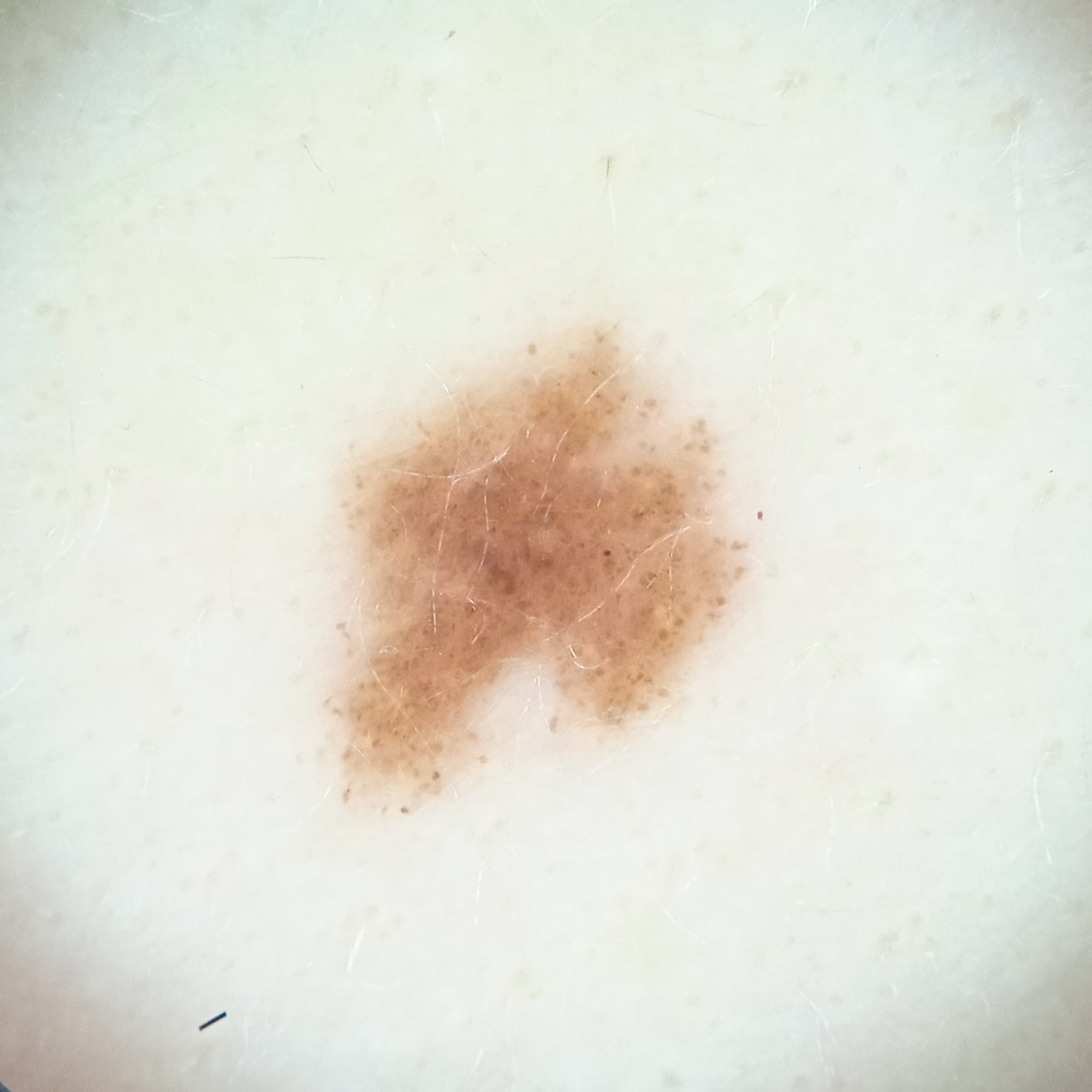Case summary:
The patient says their skin reddens with sun exposure. A moderate number of moles by the patient's own estimate. A female patient 27 years of age. Acquired for a research image collection, with no referral diagnosis. Dermoscopy of a skin lesion. The lesion is located on the back. Measuring roughly 5.9 mm.
Conclusion:
The lesion was assessed as a melanocytic nevus.